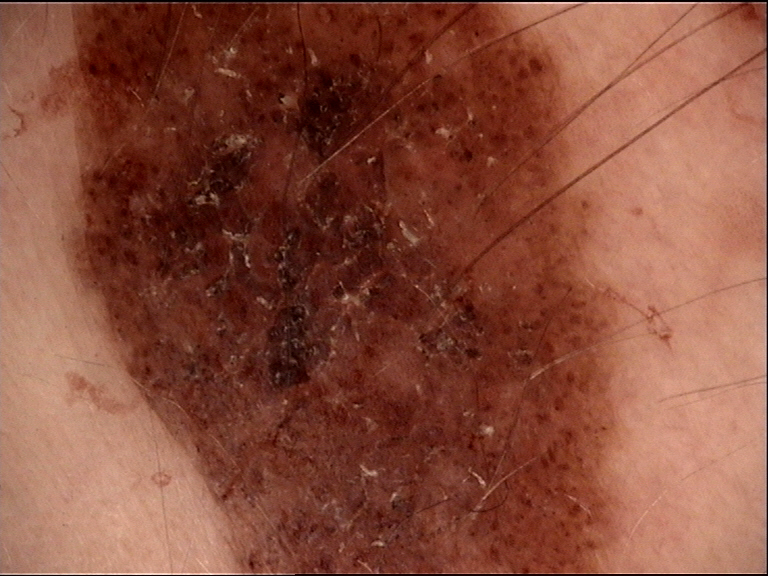Diagnosed as a banal lesion — a congenital compound nevus.